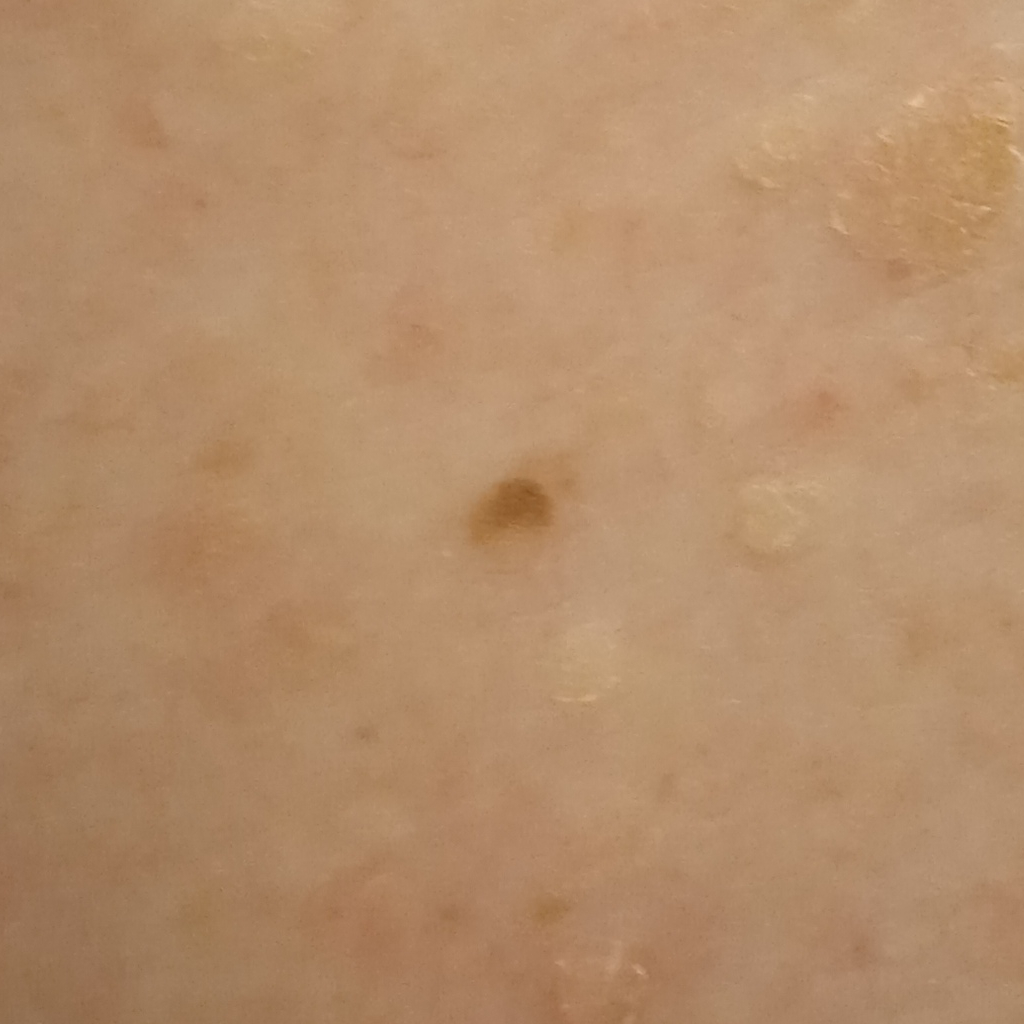A macroscopic clinical photograph of a skin lesion. Imaged for a research study, with no referral diagnosis recorded. The lesion is about 3 mm across. The consensus diagnosis for this lesion was a seborrheic keratosis.